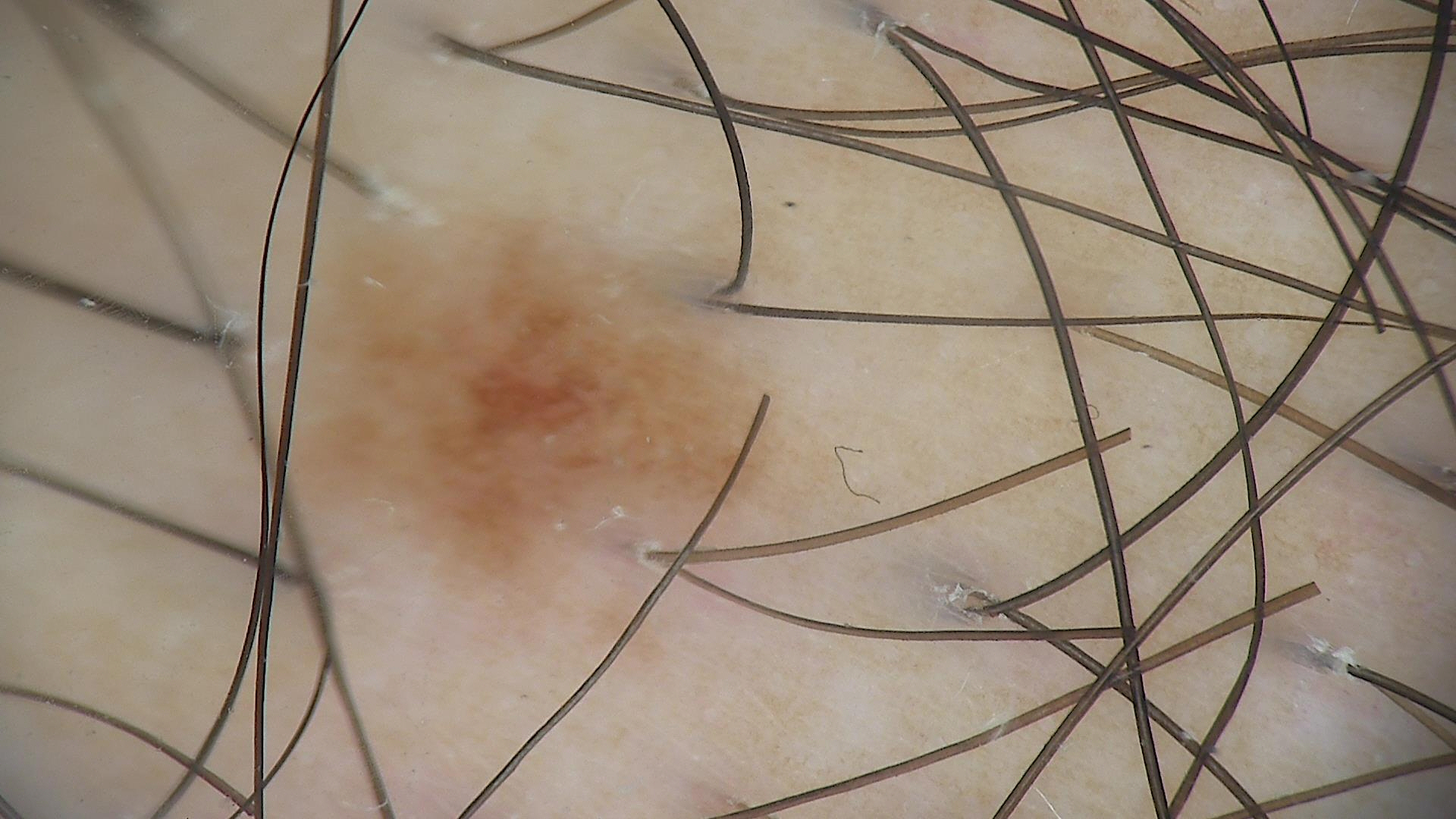{
  "image": "dermoscopy",
  "diagnosis": {
    "name": "dysplastic junctional nevus",
    "code": "jd",
    "malignancy": "benign",
    "super_class": "melanocytic",
    "confirmation": "expert consensus"
  }
}